A dermoscopic image of a skin lesion:
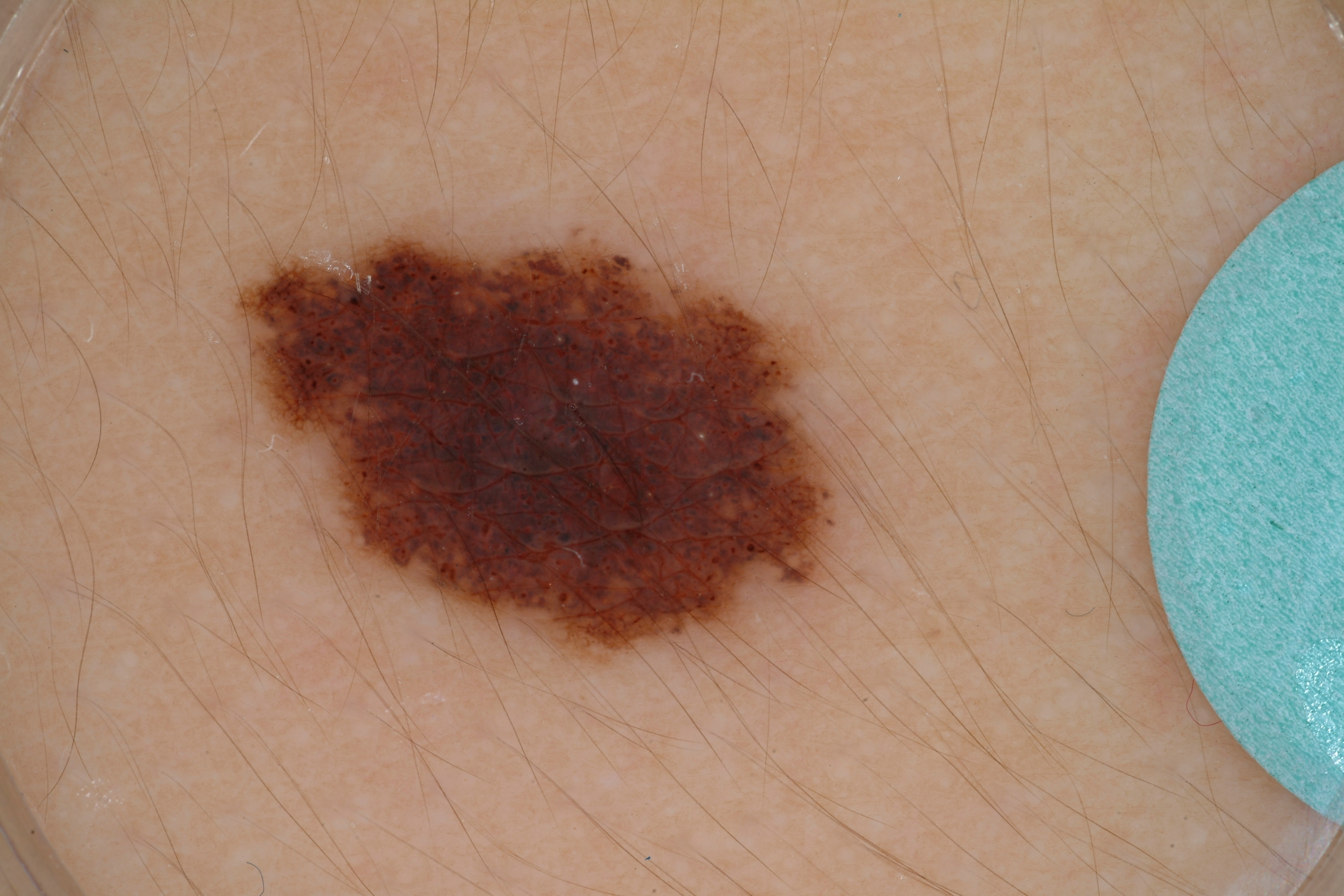| key | value |
|---|---|
| lesion bbox | x1=237, y1=213, x2=847, y2=669 |
| diagnosis | a melanocytic nevus, a benign skin lesion |